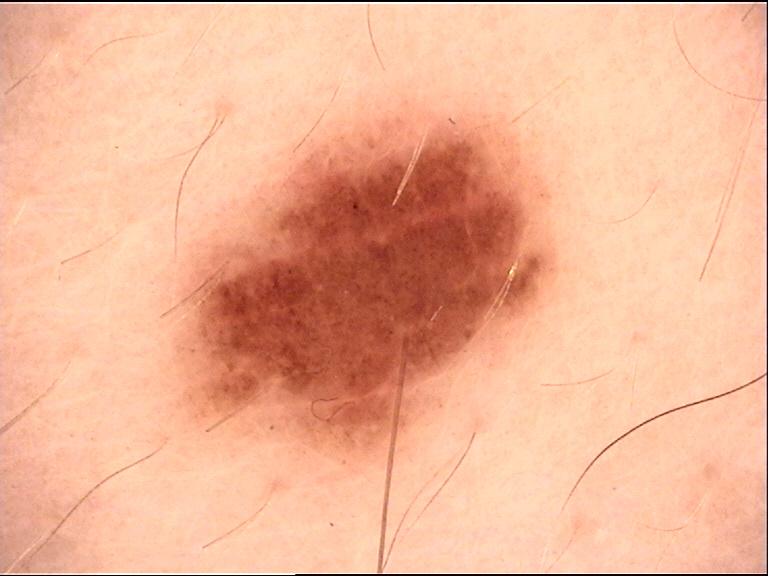A dermoscopy image of a single skin lesion.
The diagnosis was a dysplastic junctional nevus.